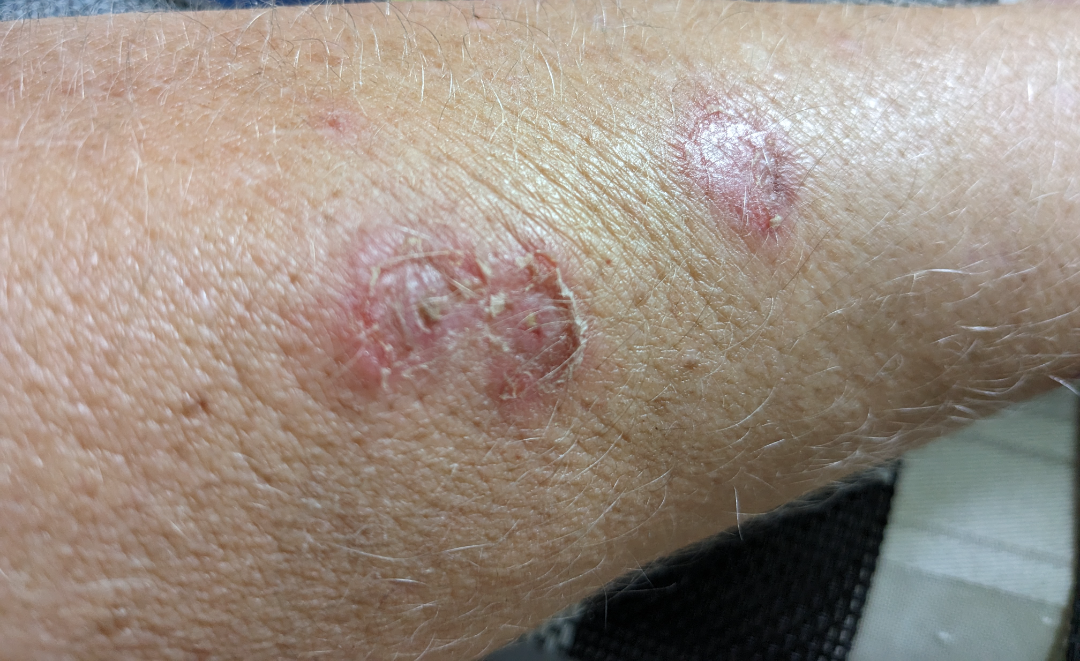Close-up view.
The lesion involves the arm.
Skin tone: Fitzpatrick II.
The lesion is described as fluid-filled and raised or bumpy.
The contributor reports the condition has been present for one to four weeks.
Most consistent with Lichen Simplex Chronicus; also consider Skin infection.